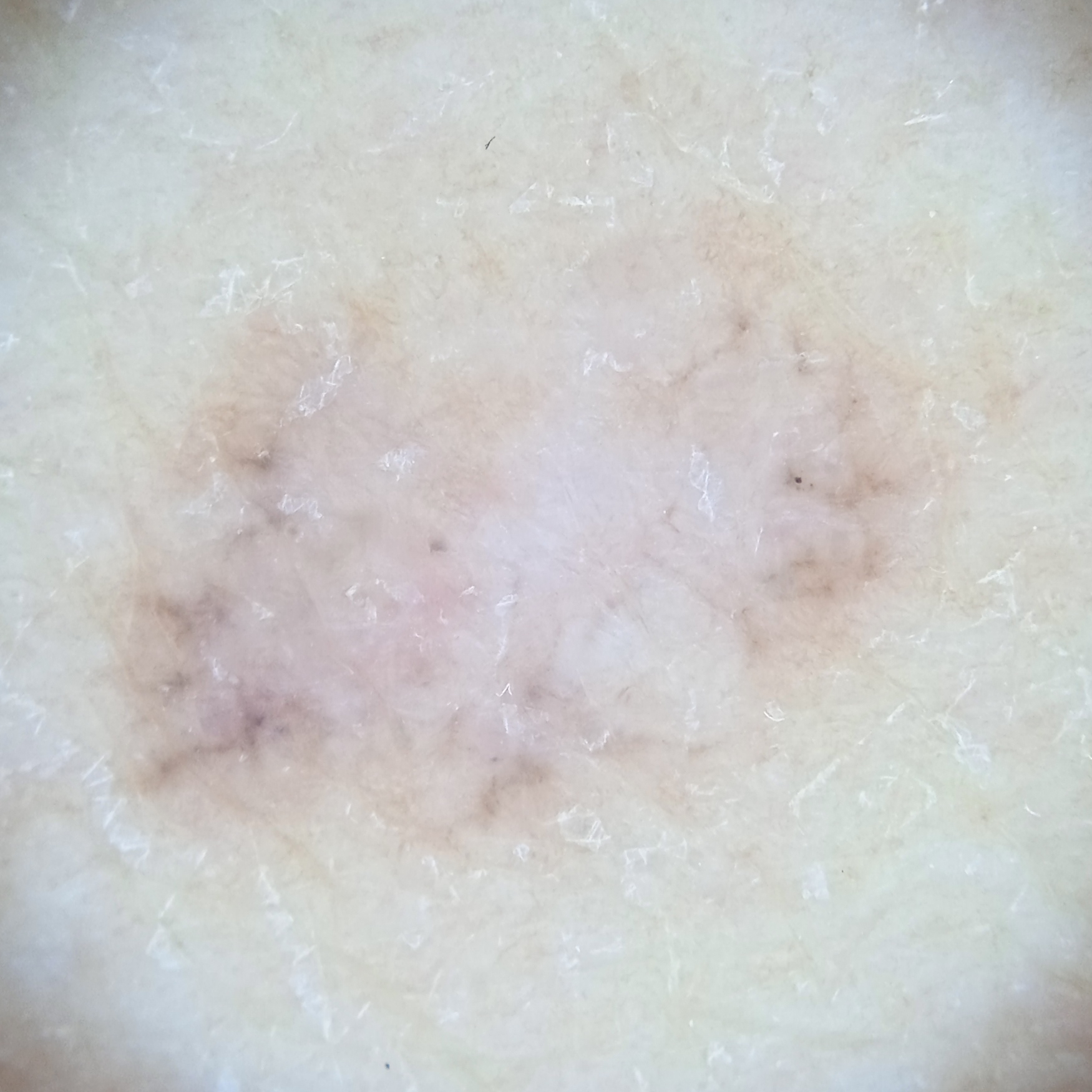The lesion was assessed as a basal cell carcinoma.